This is a close-up image: 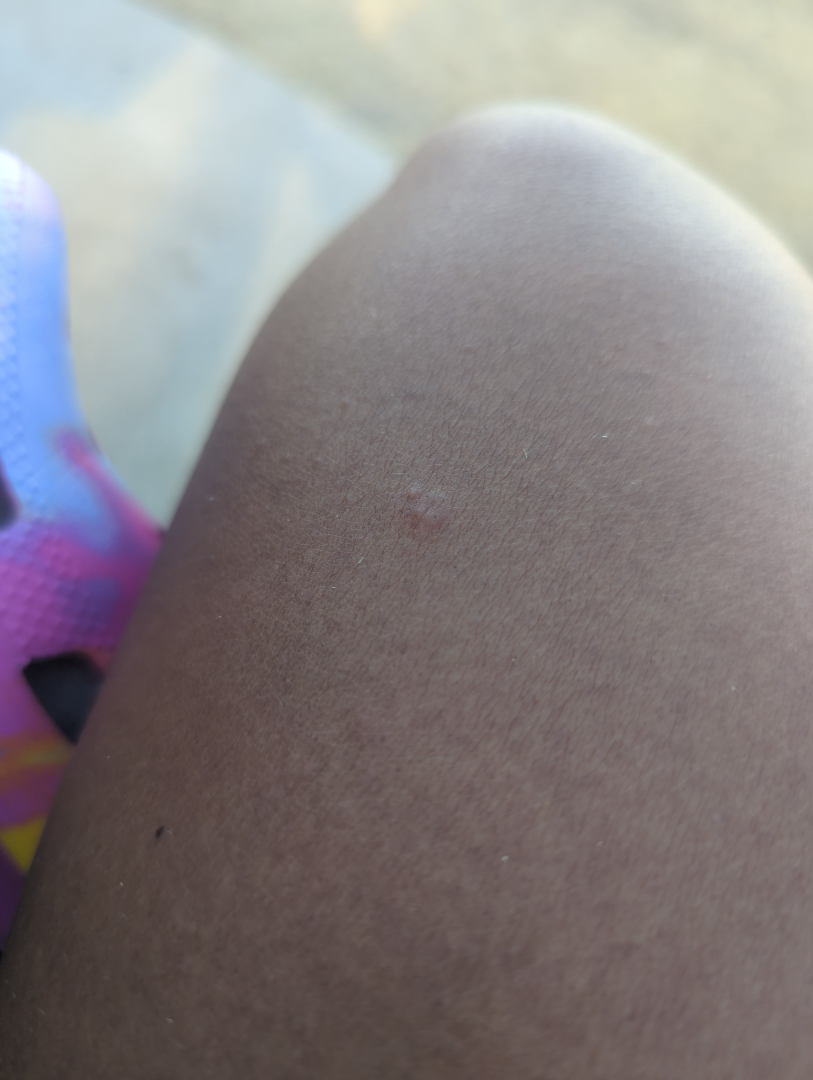assessment: could not be assessed.